A skin lesion imaged with a dermatoscope: 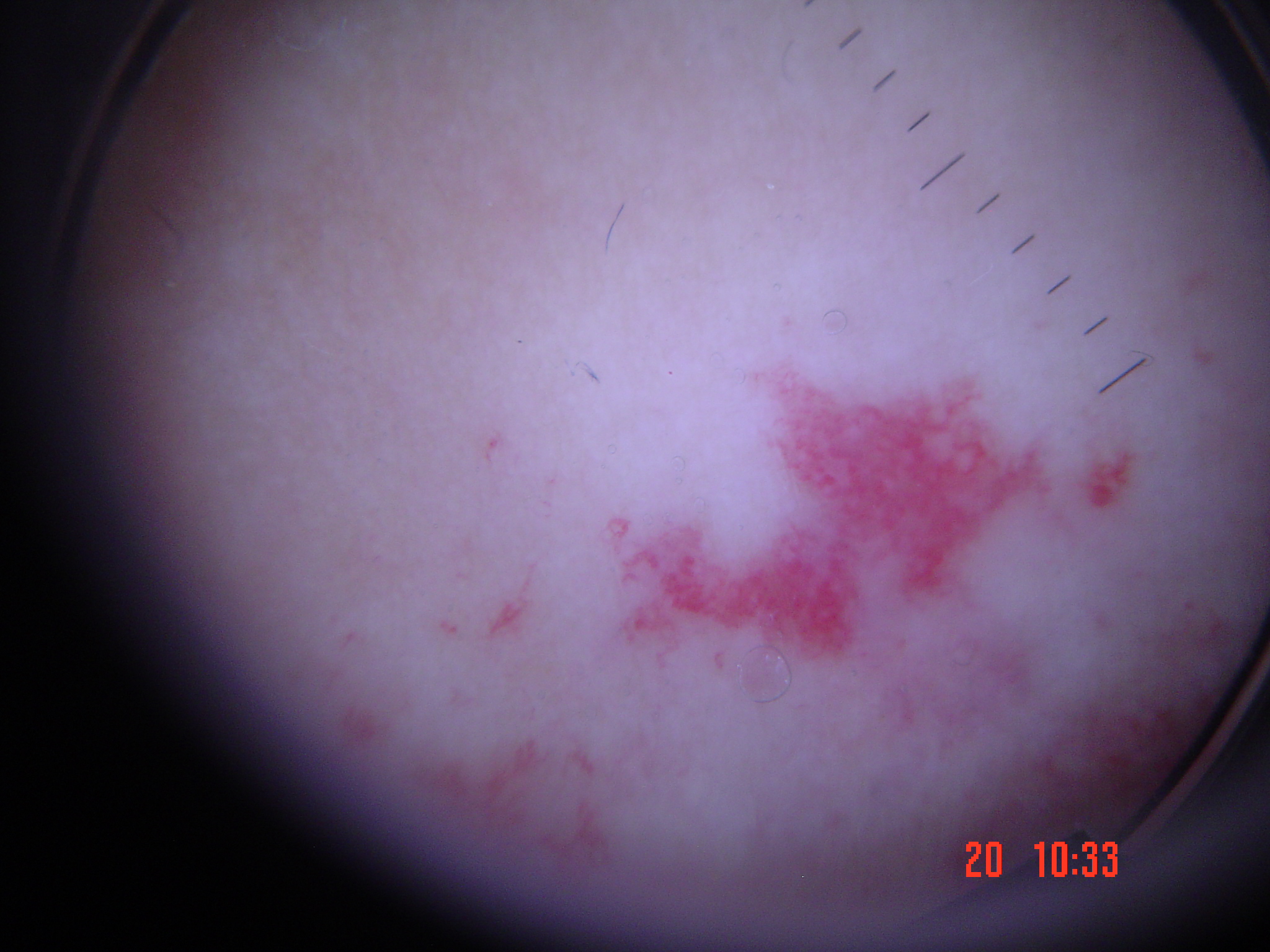  diagnosis:
    name: hemangioma
    code: ha
    malignancy: benign
    super_class: non-melanocytic
    confirmation: expert consensus